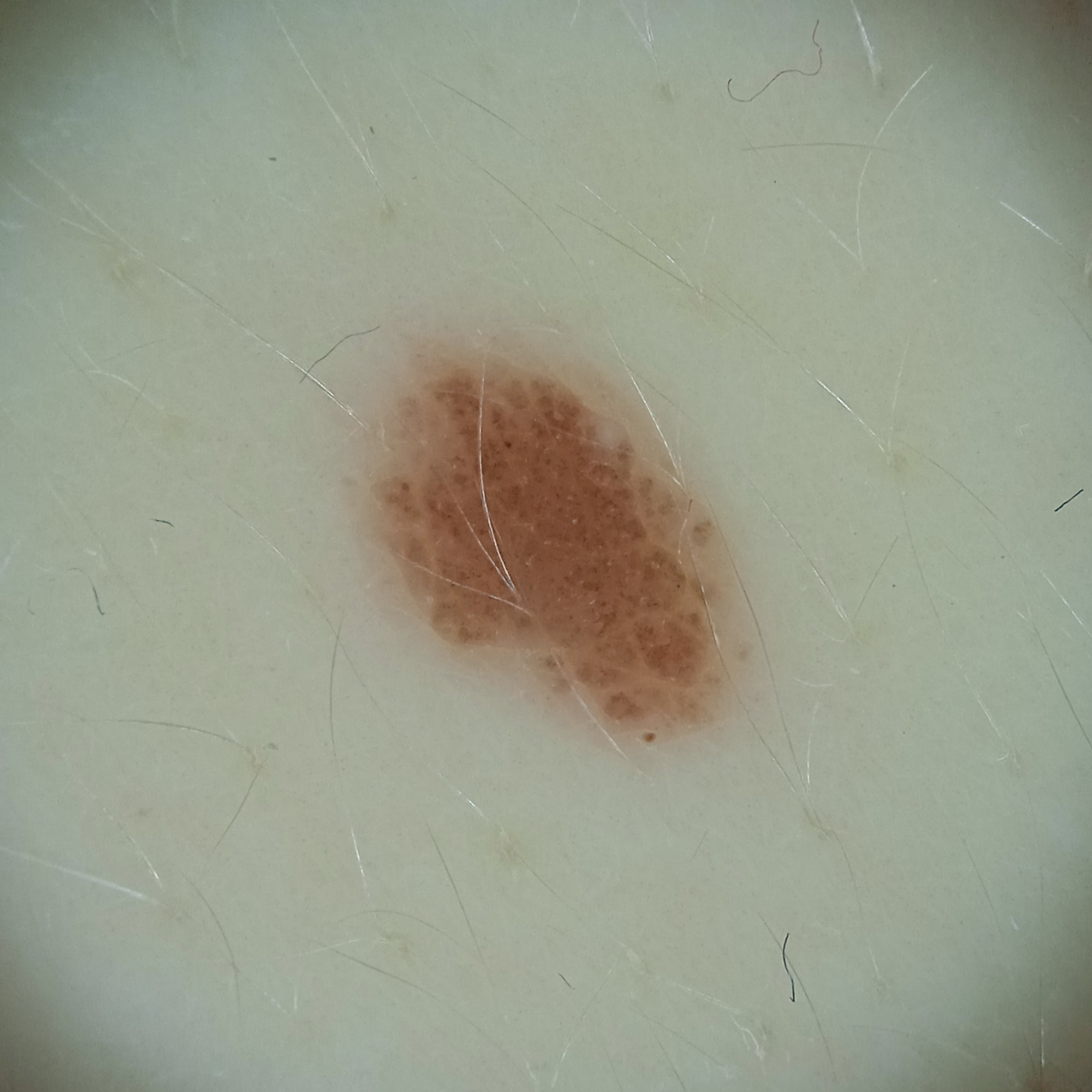| field | value |
|---|---|
| nevus count | a moderate number of melanocytic nevi |
| subject | female, age 20 |
| image | dermoscopic image |
| clinical context | research study (no referral diagnosis) |
| sun reaction | skin reddens with sun exposure |
| anatomic site | the torso |
| lesion size | 5.1 mm |
| diagnostic label | melanocytic nevus (dermatologist consensus) |